A patient 69 years old — 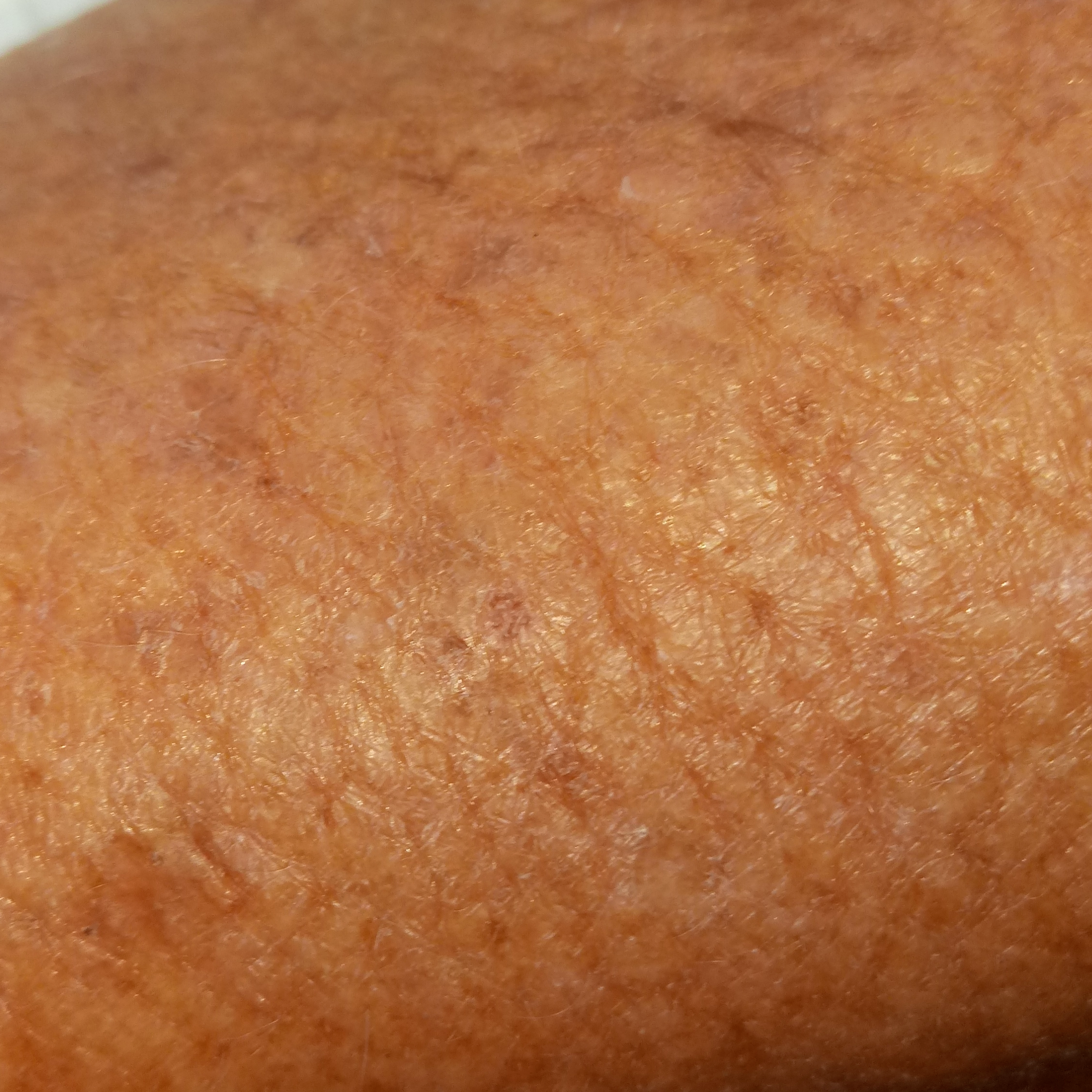patient-reported symptoms: itching / no change in appearance, no growth; diagnostic label: actinic keratosis (clinical consensus).